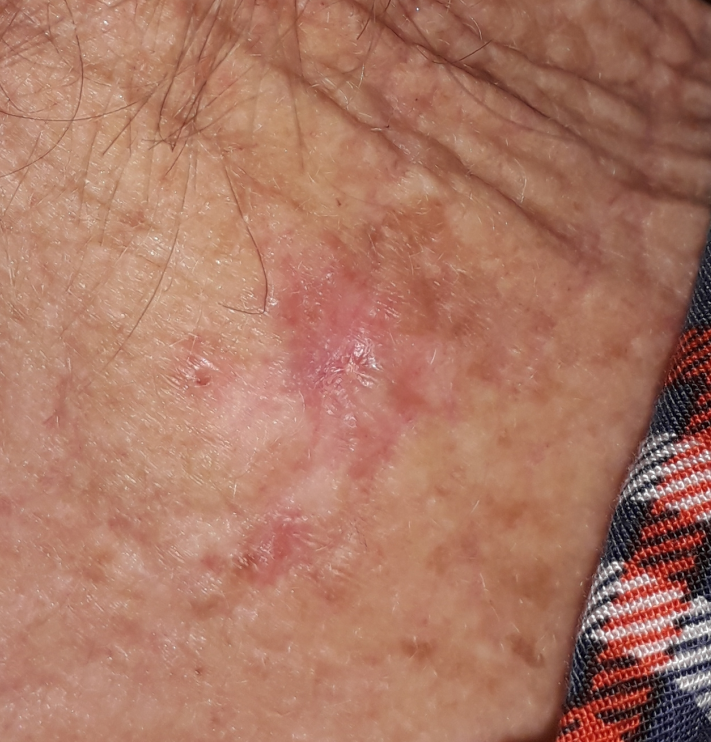Clinical context: The chart notes prior skin cancer (patient or family), prior malignancy (patient or family), and pesticide exposure. FST III. The lesion is on the neck. Measuring about 25 × 13 mm. By the patient's account, the lesion has grown and hurts, but has not changed and has not bled. Diagnosis: Histopathologically confirmed as a basal cell carcinoma.